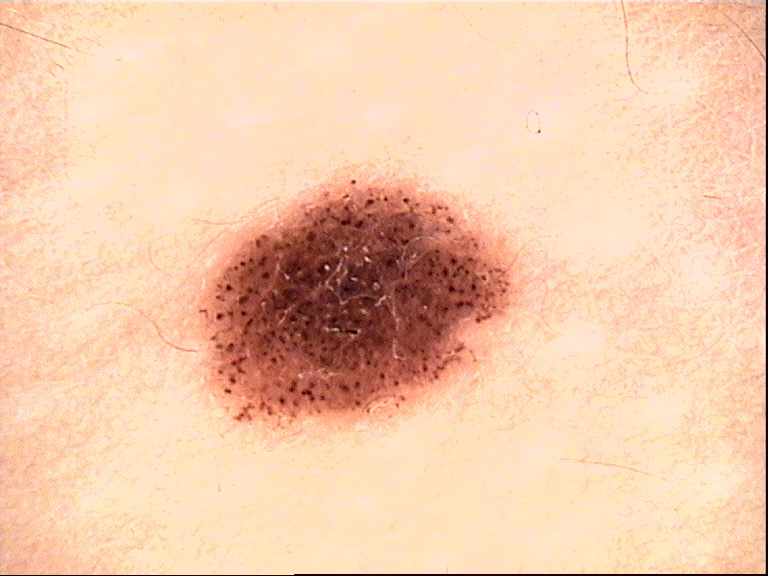A dermoscopic image of a skin lesion. The architecture is that of a banal lesion. The diagnostic label was a compound nevus.